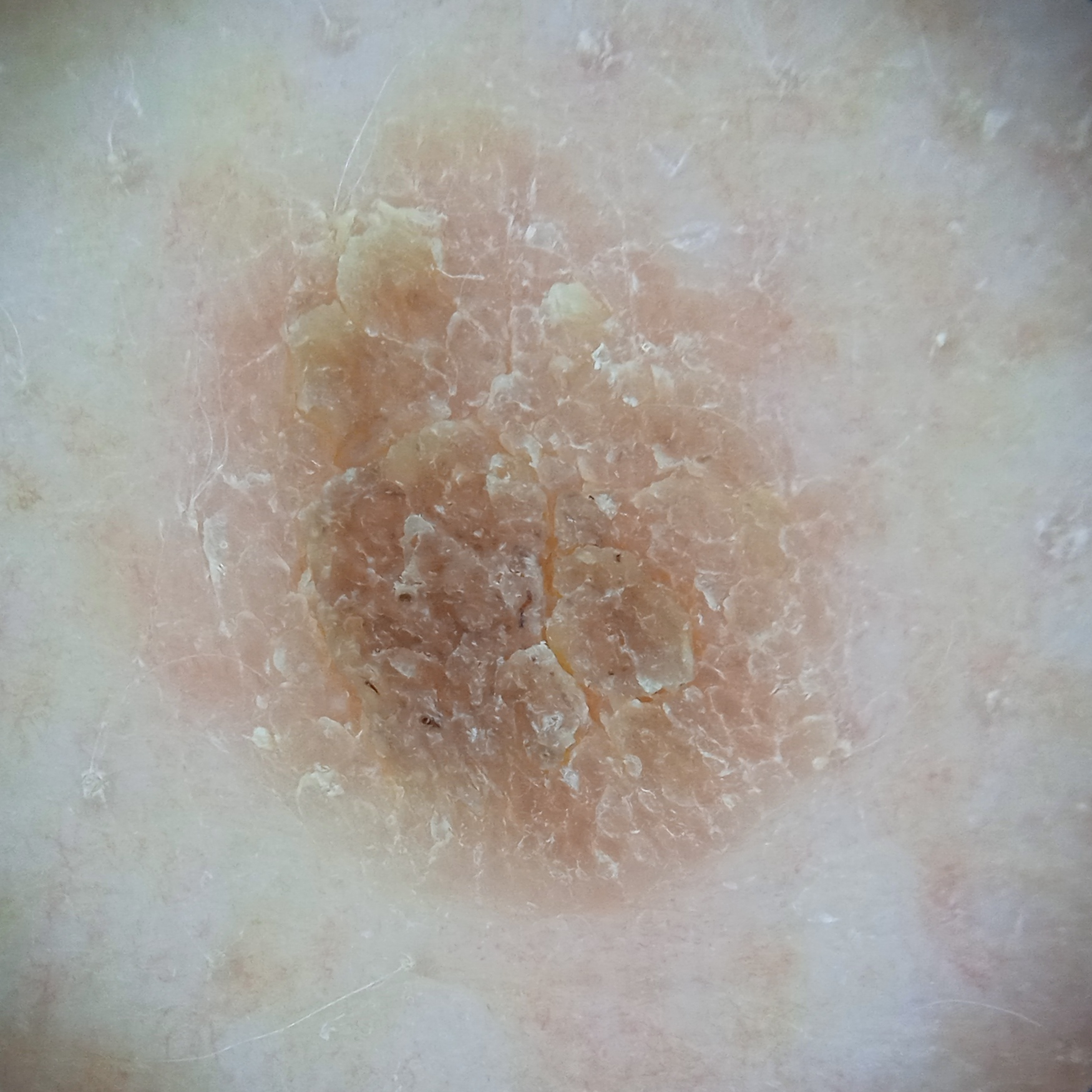A female subject 73 years of age. Imaged for a research study, with no referral diagnosis recorded. The lesion is on the back. The lesion measures approximately 8.6 mm. Dermatologist review favored a seborrheic keratosis.